The patient is 18–29, male. The head or neck is involved. An image taken at a distance.
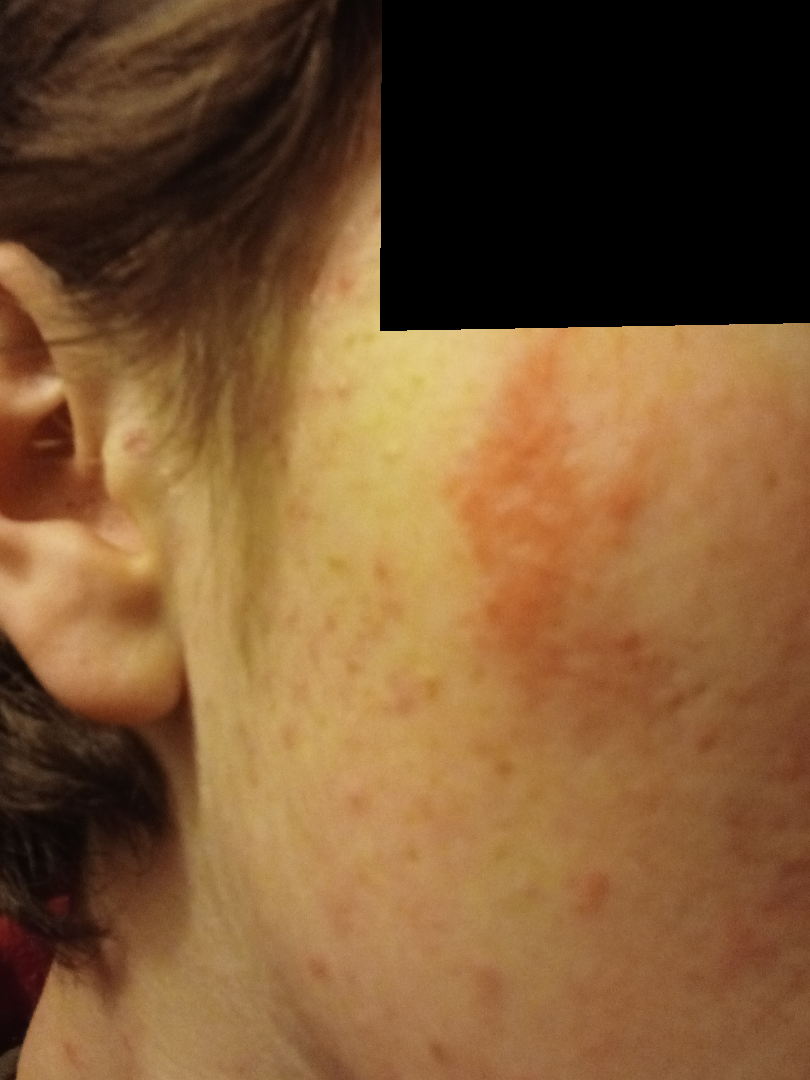<report>
  <symptoms>itching, bothersome appearance</symptoms>
  <duration>about one day</duration>
  <differential>
    <leading>Acne</leading>
    <considered>Irritant Contact Dermatitis</considered>
  </differential>
</report>